A female subject, in their mid-30s. A skin lesion imaged with a dermatoscope — 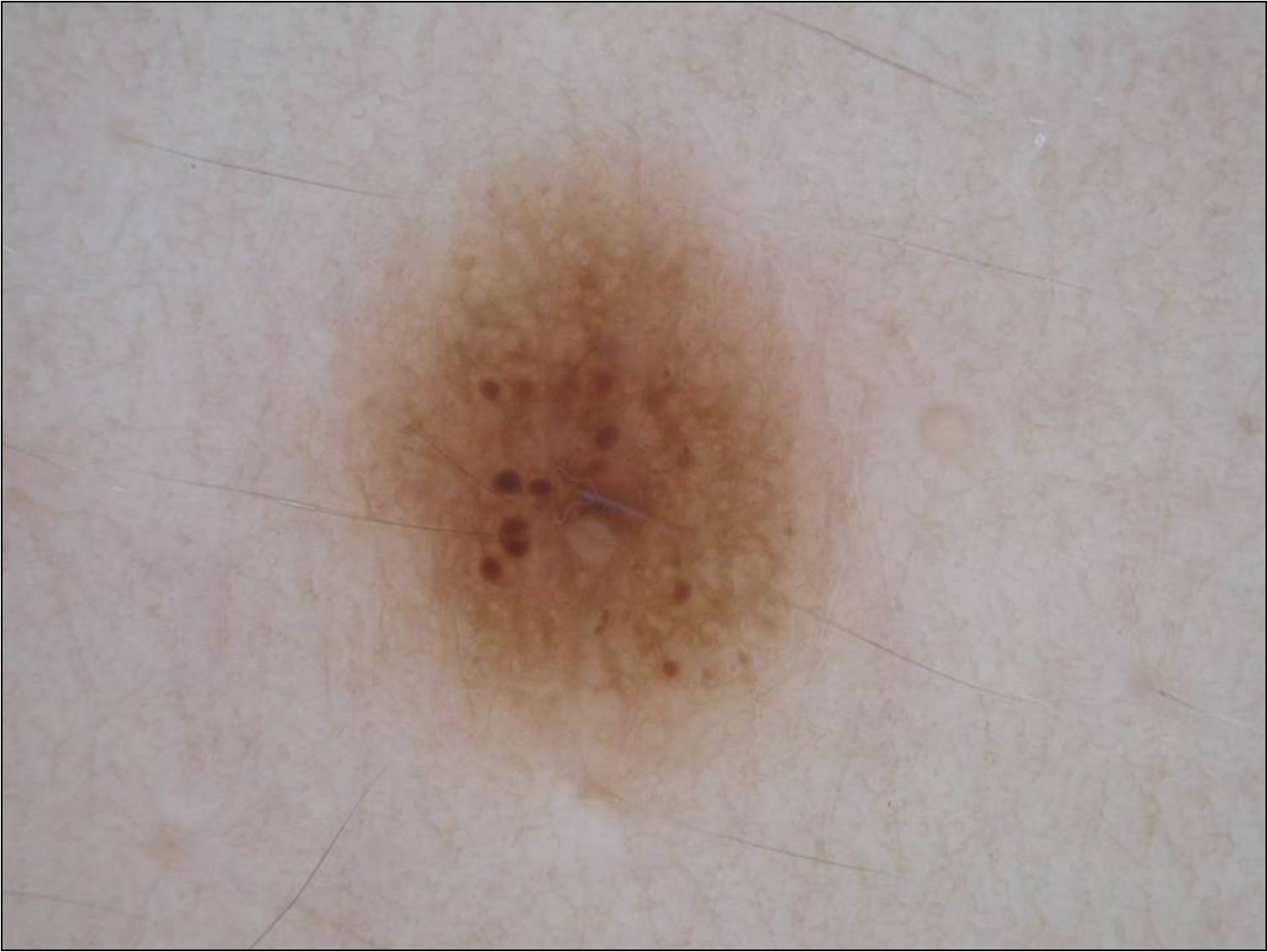dermoscopic findings: pigment network
lesion extent: moderate
lesion location: box(334, 157, 846, 801)
diagnostic label: a melanocytic nevus